A dermoscopic photograph of a skin lesion: 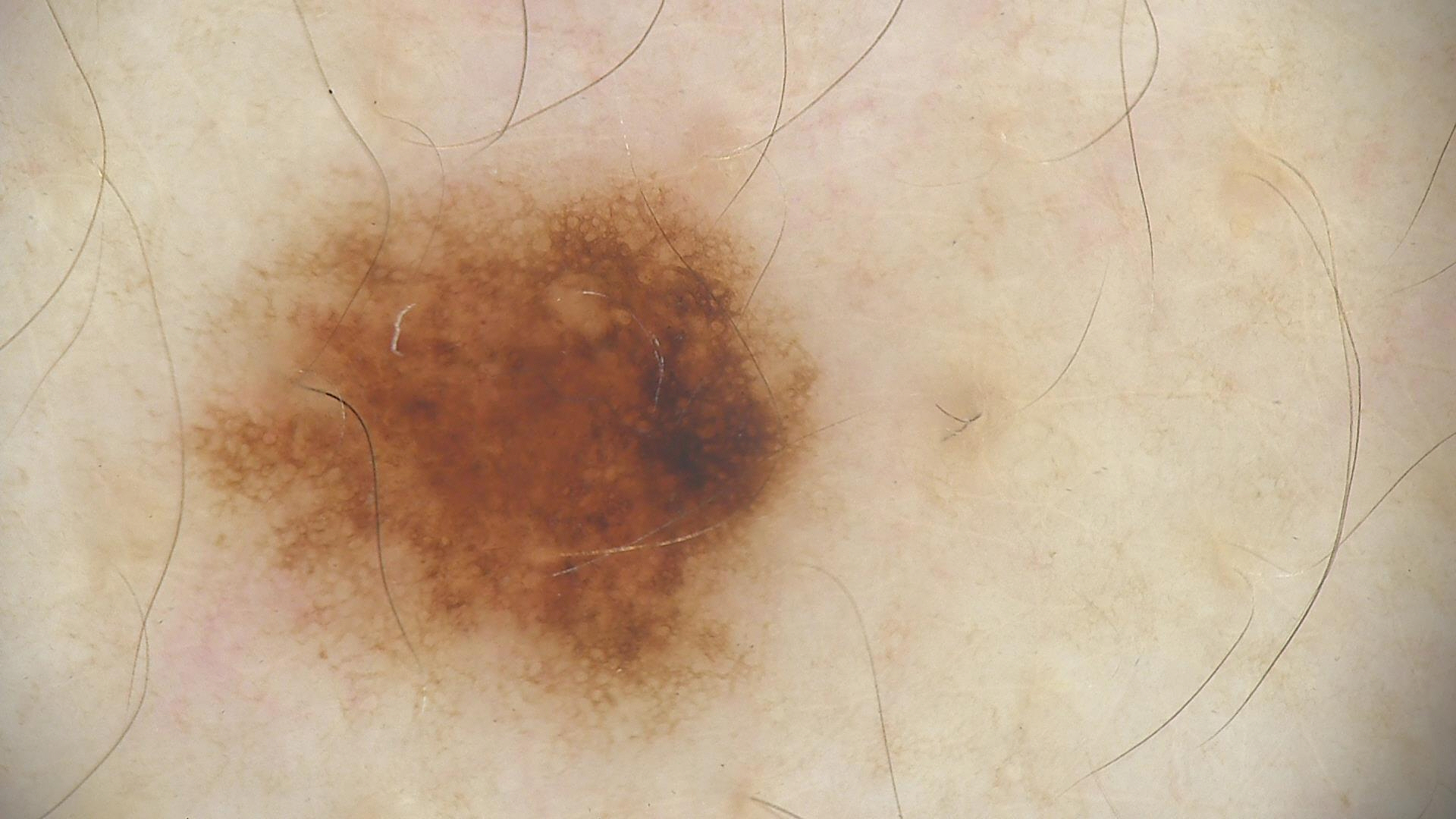Case:
* diagnostic label: dysplastic junctional nevus (expert consensus)